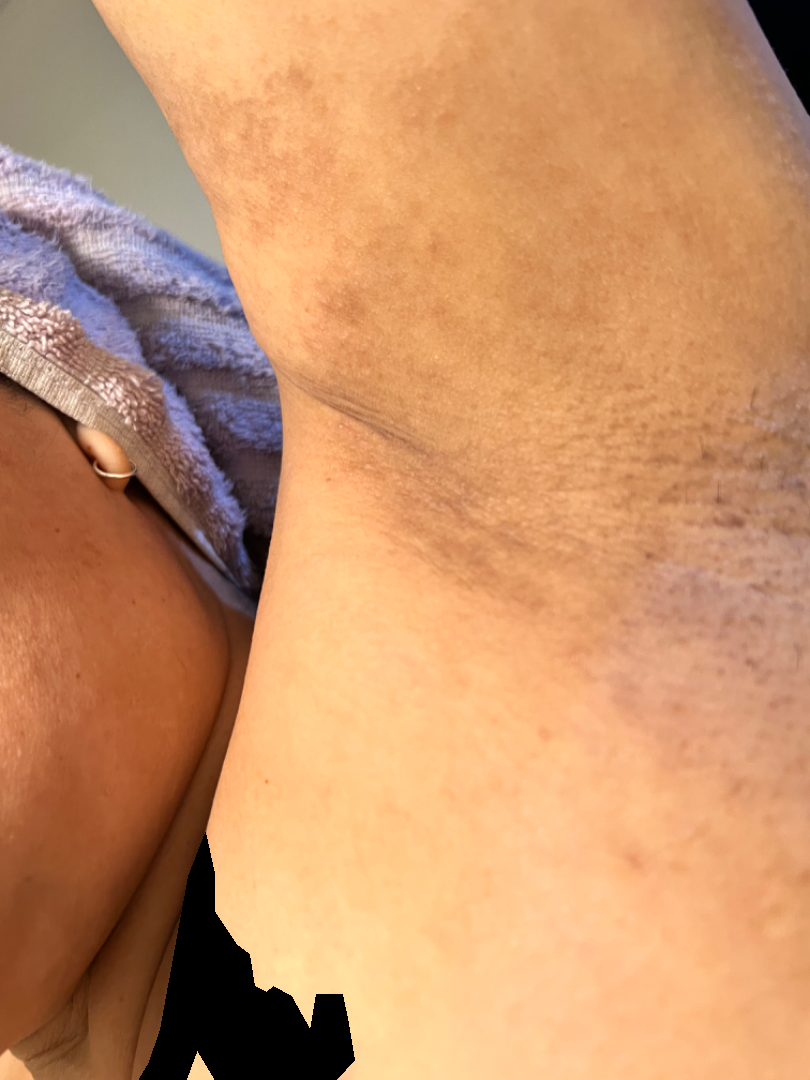{
  "shot_type": "close-up",
  "body_site": [
    "arm",
    "front of the torso"
  ],
  "differential": {
    "leading": [
      "Allergic Contact Dermatitis"
    ],
    "considered": [
      "Irritant Contact Dermatitis"
    ]
  }
}